Male subject, age 40–49; the photograph was taken at a distance; the affected area is the back of the hand: 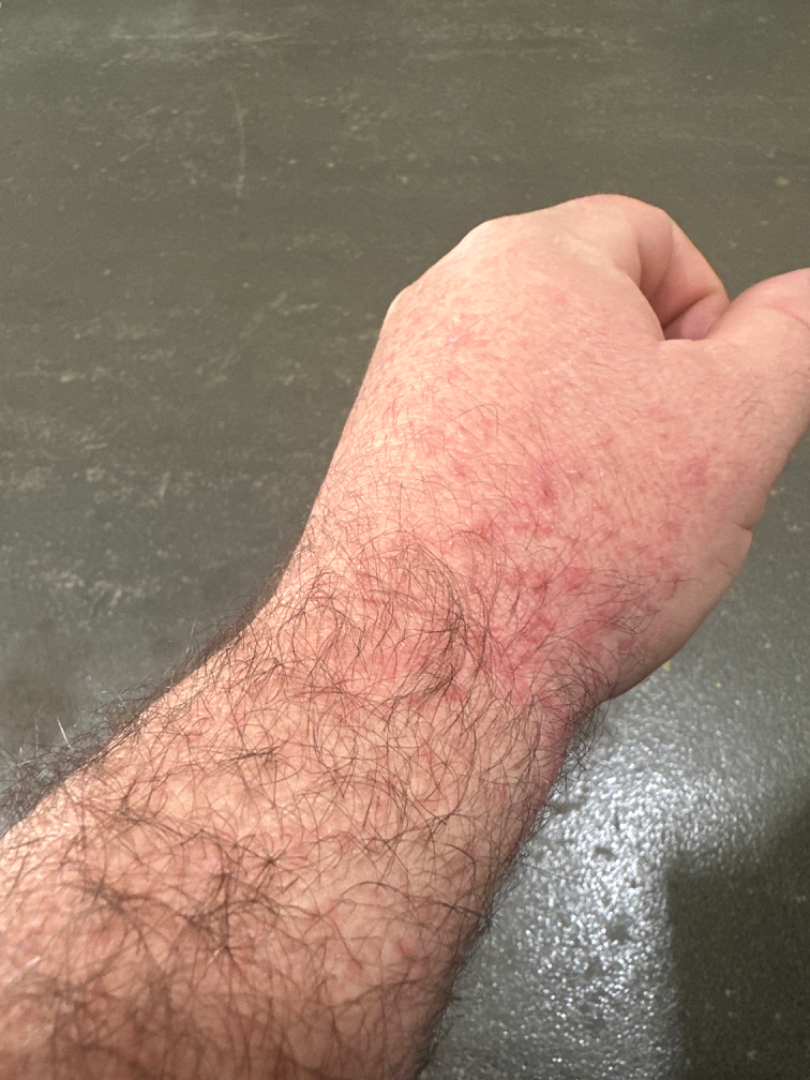A single dermatologist reviewed the case: Folliculitis, Eczema and Allergic Contact Dermatitis were each considered, in no particular order.